Close-up view: 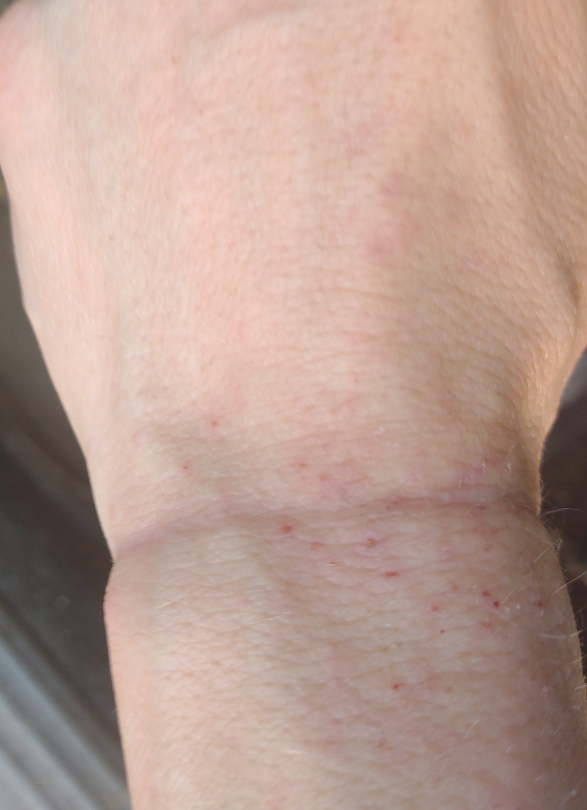Findings:
* assessment: not assessable